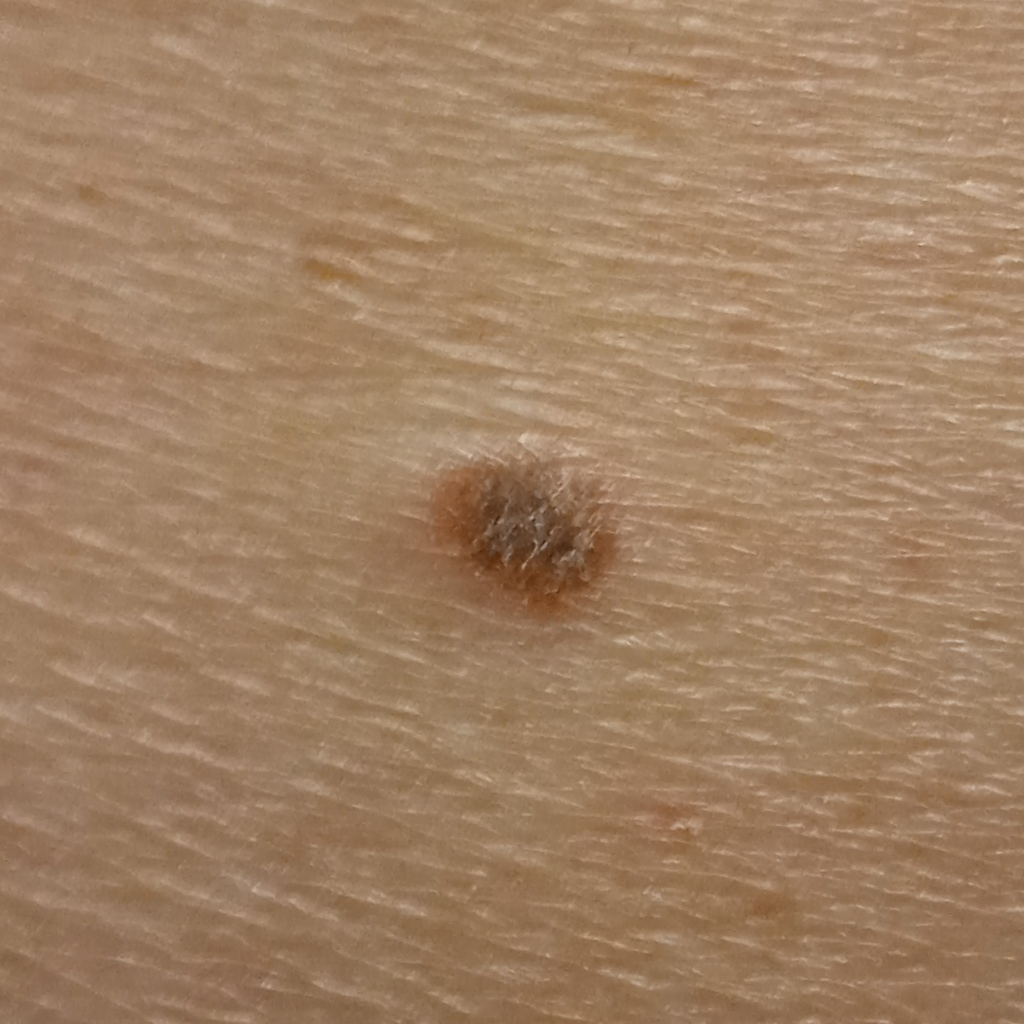A clinical photograph of a skin lesion. The patient says their skin tans without first burning. Collected as part of a research study, without a referral diagnosis. A male subject aged 79. The lesion is about 5.9 mm across. The diagnostic impression was a seborrheic keratosis.